A dermoscopic photograph of a skin lesion.
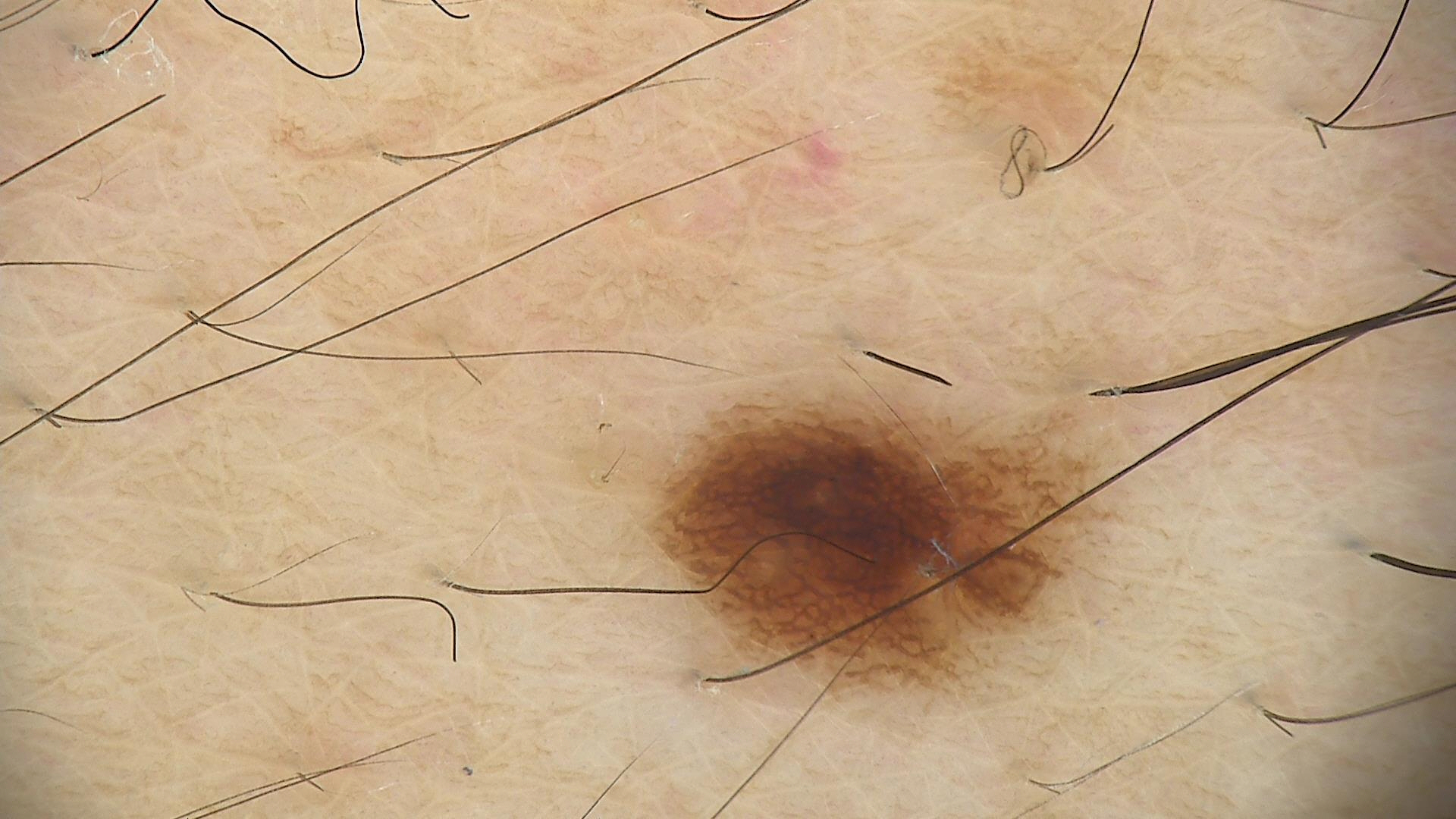The diagnostic label was a dysplastic junctional nevus.